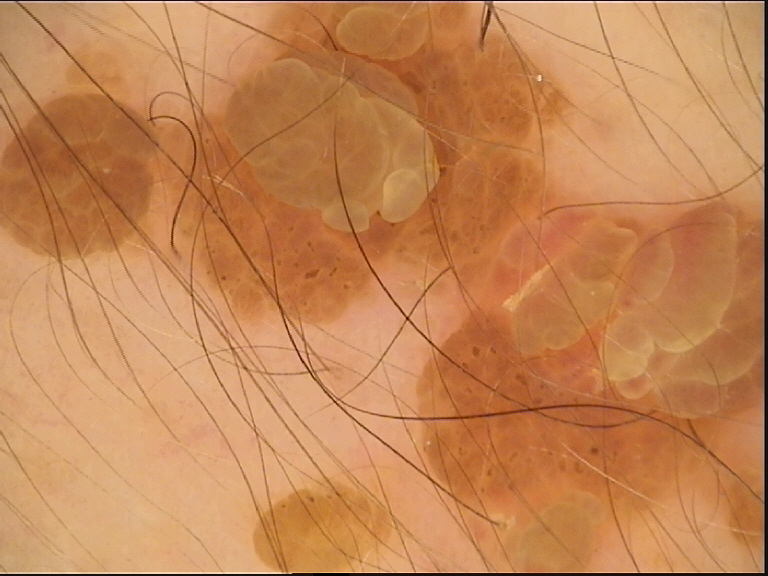Diagnosed as a seborrheic keratosis.